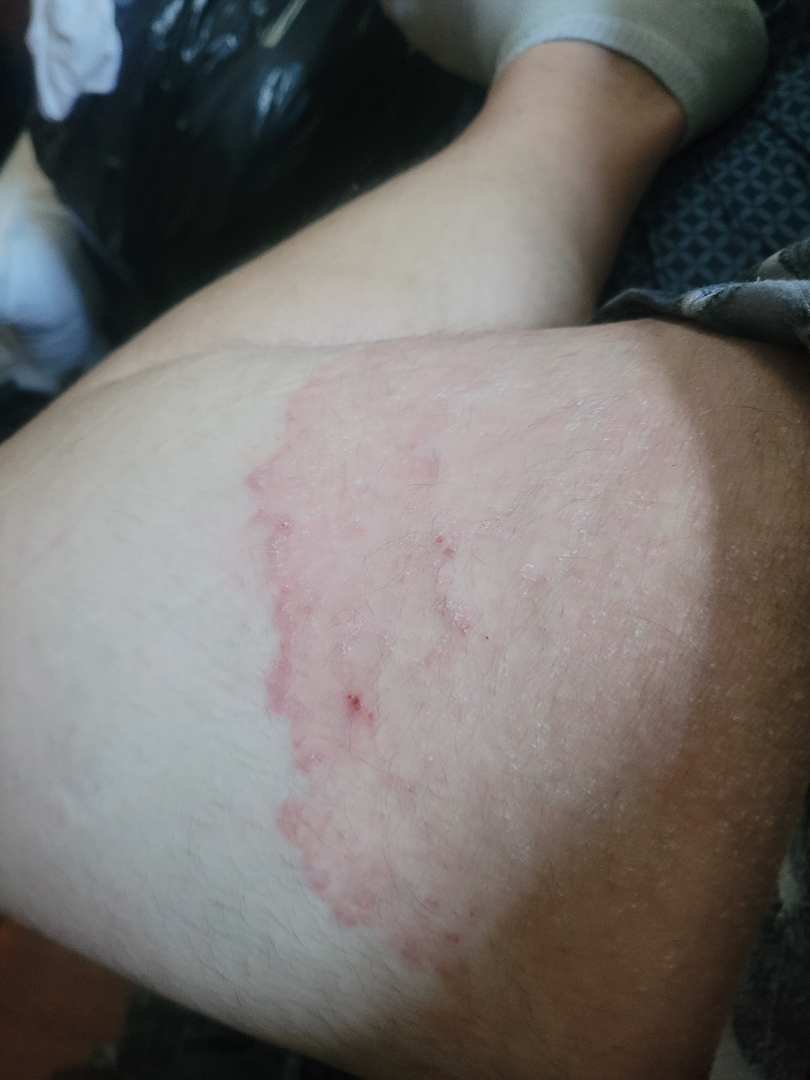patient: male, age 40–49
shot_type: close-up
body_site:
  - leg
  - head or neck
differential:
  leading:
    - Tinea